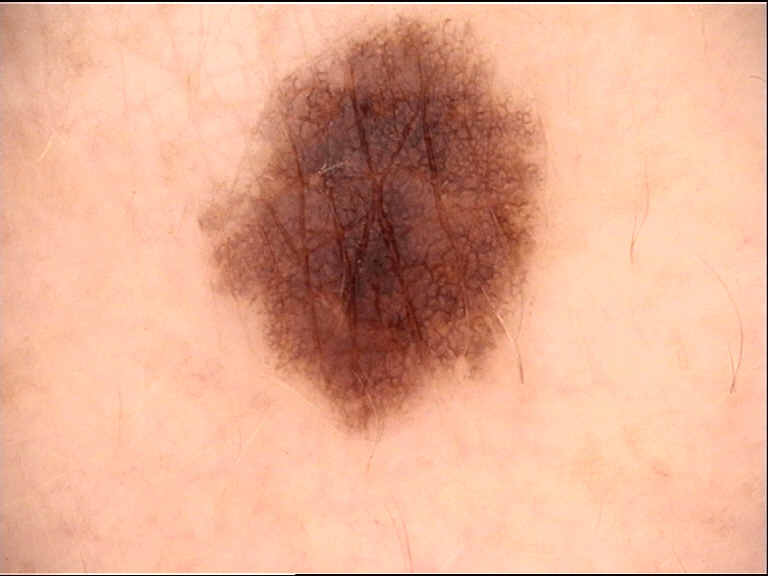assessment: dysplastic junctional nevus (expert consensus).